A dermoscopic photograph of a skin lesion · the chart records a prior melanoma · Fitzpatrick II.
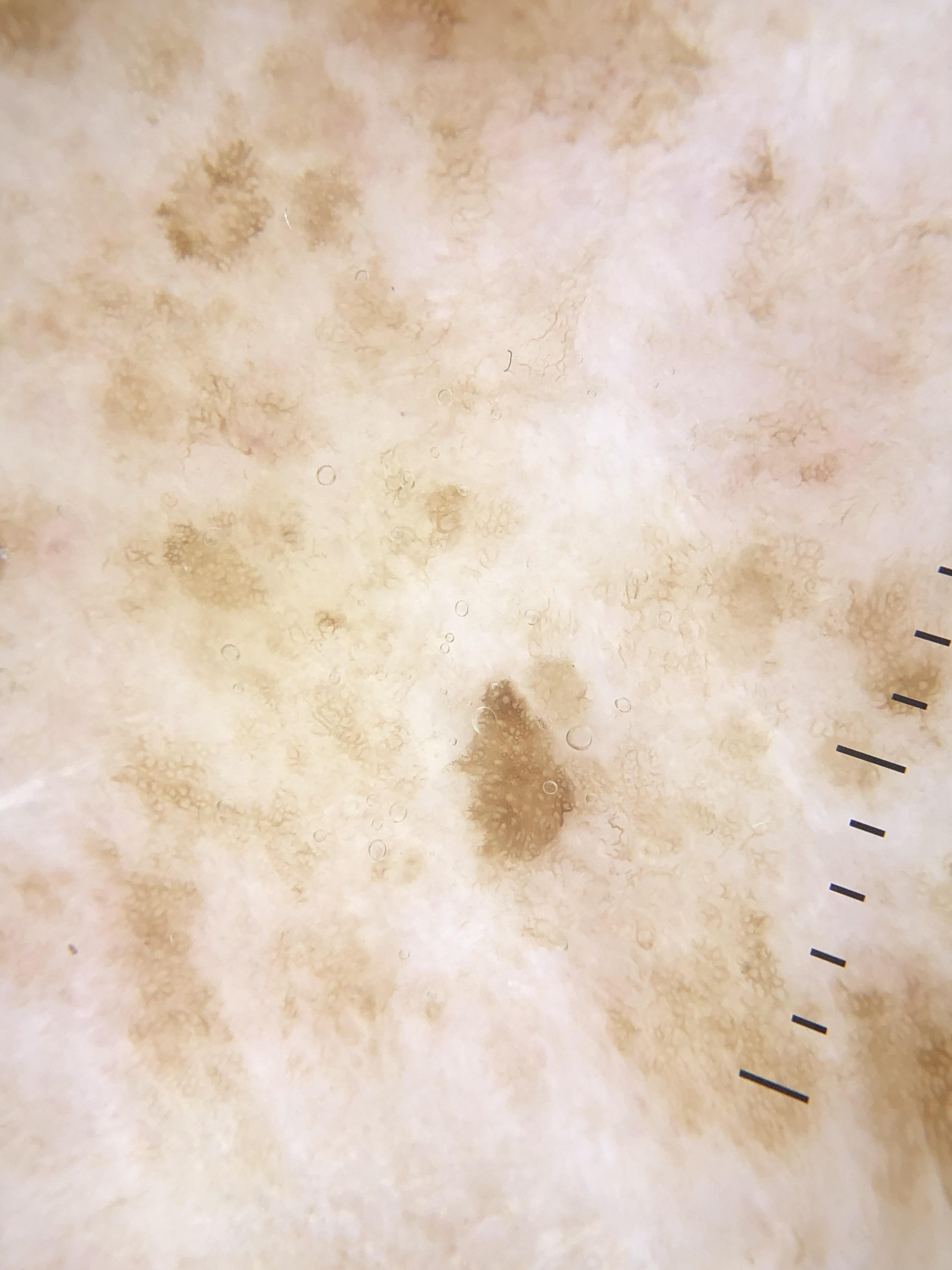The lesion was found on a lower extremity.
Histopathological examination showed a lesion of melanocytic origin — a nevus.